The patient is 50–59, female; located on the leg; the photo was captured at an angle.
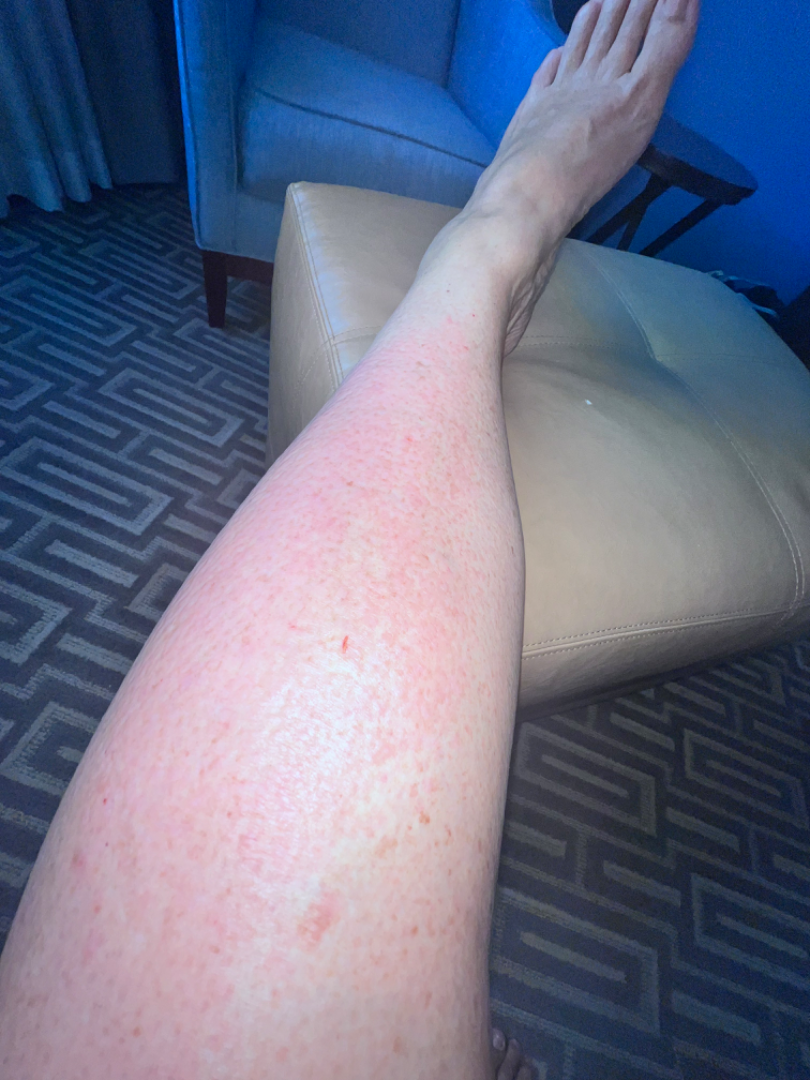Findings:
– patient's own categorization · a rash
– lesion symptoms · darkening, bothersome appearance and itching
– skin tone · non-clinician graders estimated Monk Skin Tone 1 or 2
– history · three to twelve months
– other reported symptoms · joint pain and fatigue
– impression · Allergic Contact Dermatitis (54%); Amyloidosis of skin (23%); Pretibial myxedema (23%)